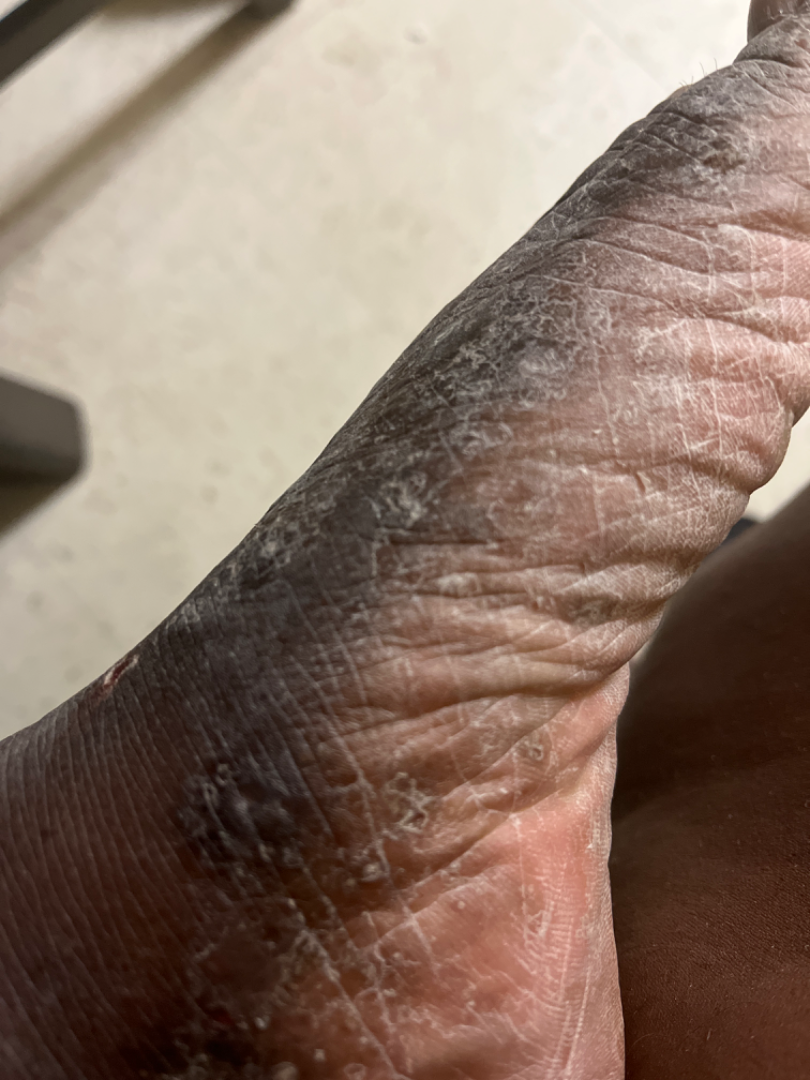Q: Where on the body?
A: top or side of the foot
Q: Age and sex?
A: female, age 30–39
Q: What is the framing?
A: close-up
Q: What is the dermatologist's impression?
A: the differential, in no particular order, includes Tinea and Eczema; a more distant consideration is Psoriasis